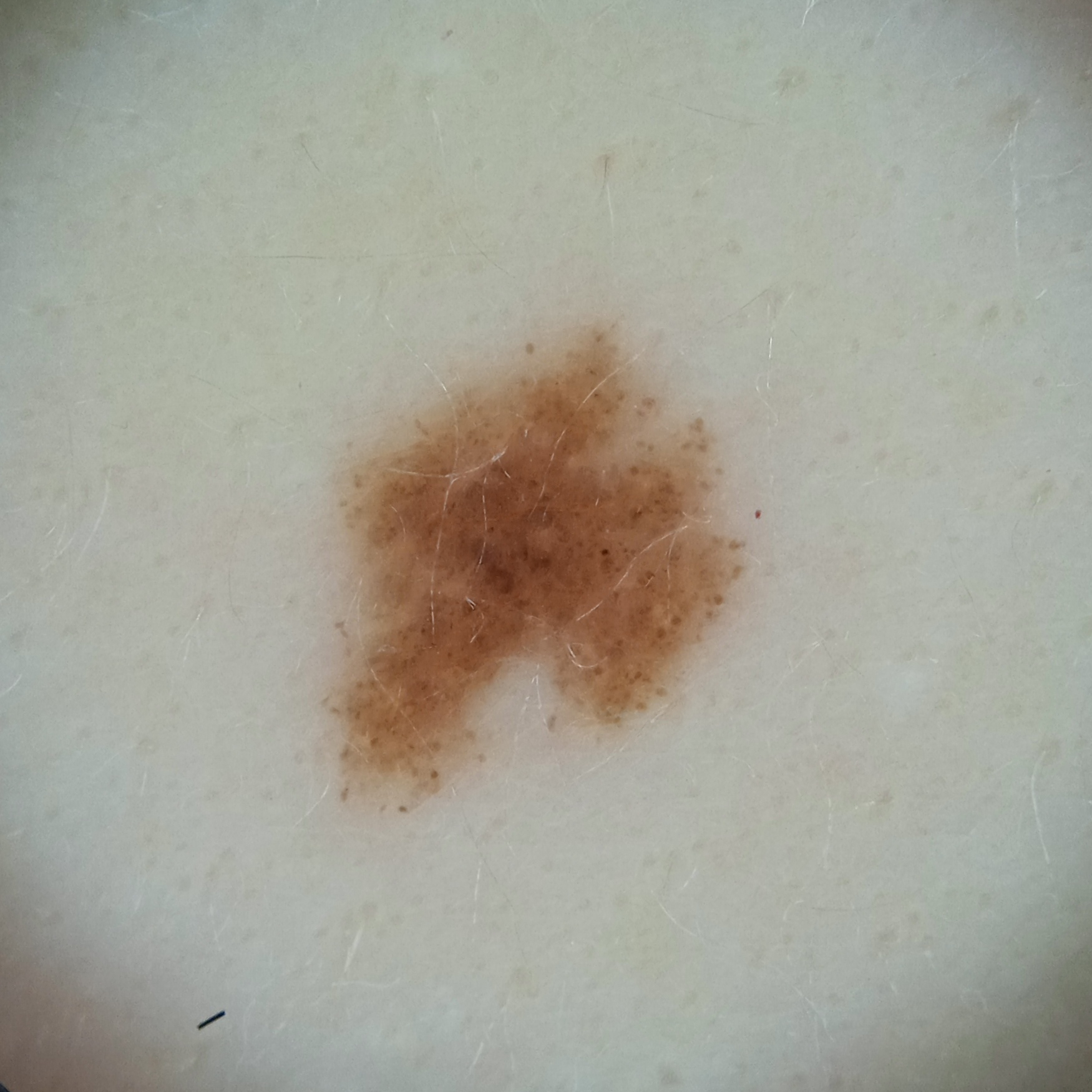Summary: Acquired for a research image collection, with no referral diagnosis. The patient reports no sunbed use and no family history of skin cancer. A dermoscopy image of a skin lesion. The patient says their skin reddens with sun exposure. A female subject 27 years old. The lesion is on the back. Assessment: The diagnostic impression was a melanocytic nevus.